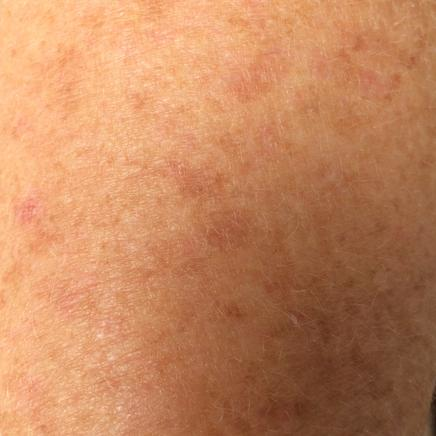Patient and lesion:
A smartphone photograph of a skin lesion. The lesion was found on a forearm. The patient describes that the lesion does not itch and has not bled.
Conclusion:
The clinical impression was a lesion of indeterminate malignant potential — an actinic keratosis.